The patient says their skin reddens with sun exposure. The patient describes having few moles overall. A male patient 76 years old. A clinical photograph showing a skin lesion: 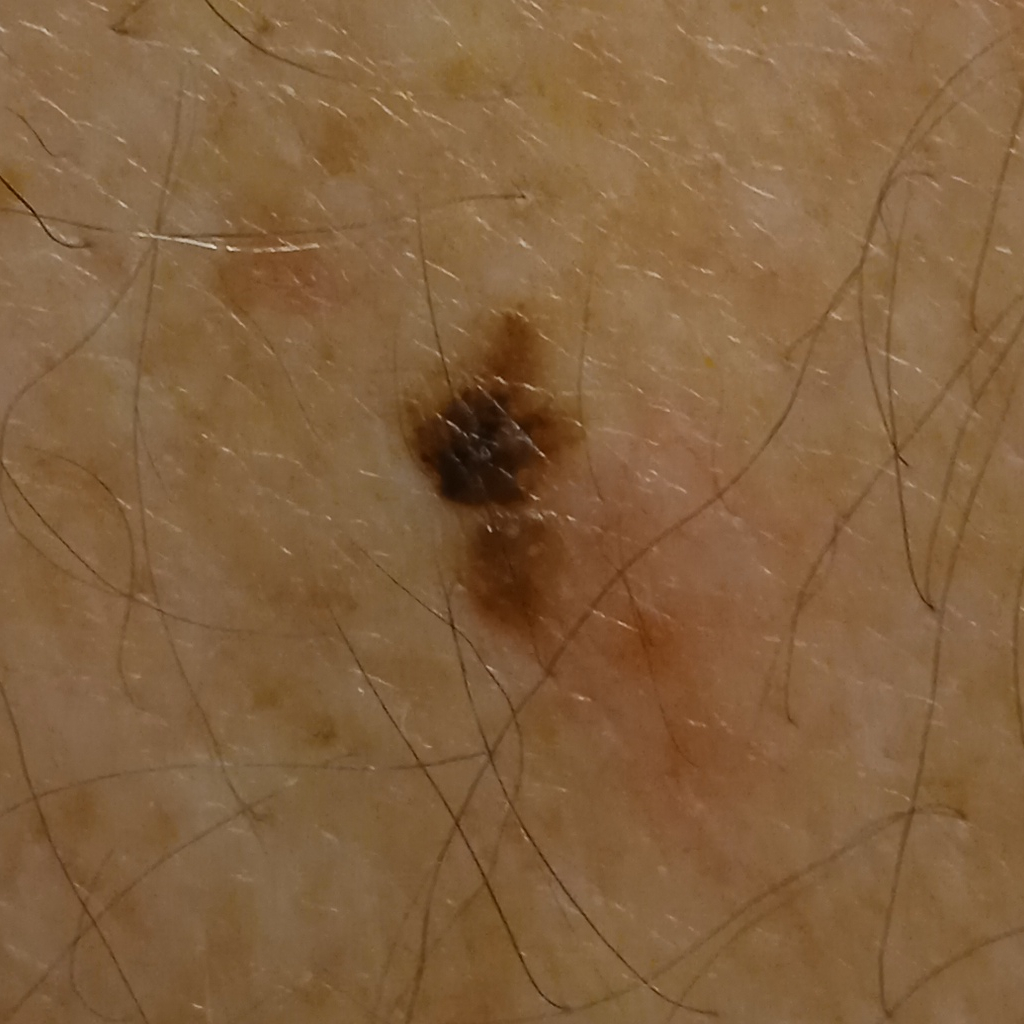Clinical context:
The lesion is located on the back. Measuring roughly 7.8 mm.
Conclusion:
Dermatologist review favored a seborrheic keratosis.